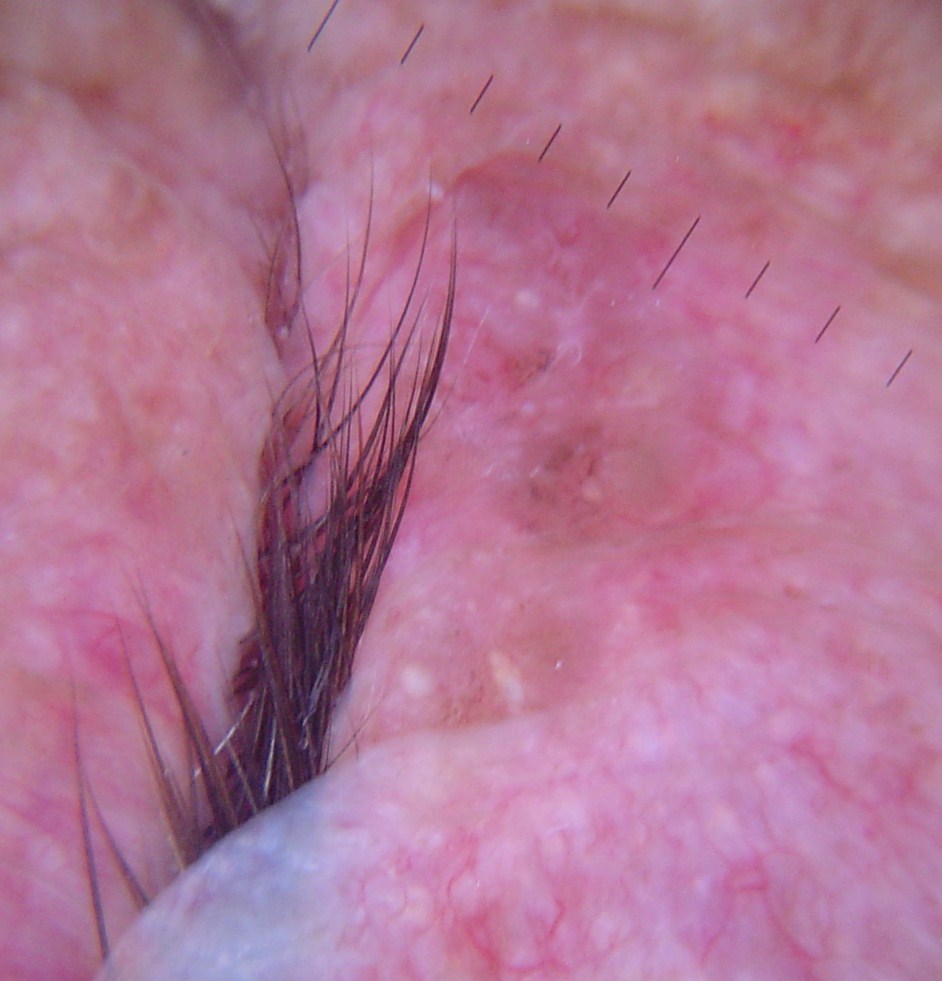{
  "diagnosis": {
    "name": "basal cell carcinoma",
    "code": "bcc",
    "malignancy": "malignant",
    "super_class": "non-melanocytic",
    "confirmation": "histopathology"
  }
}